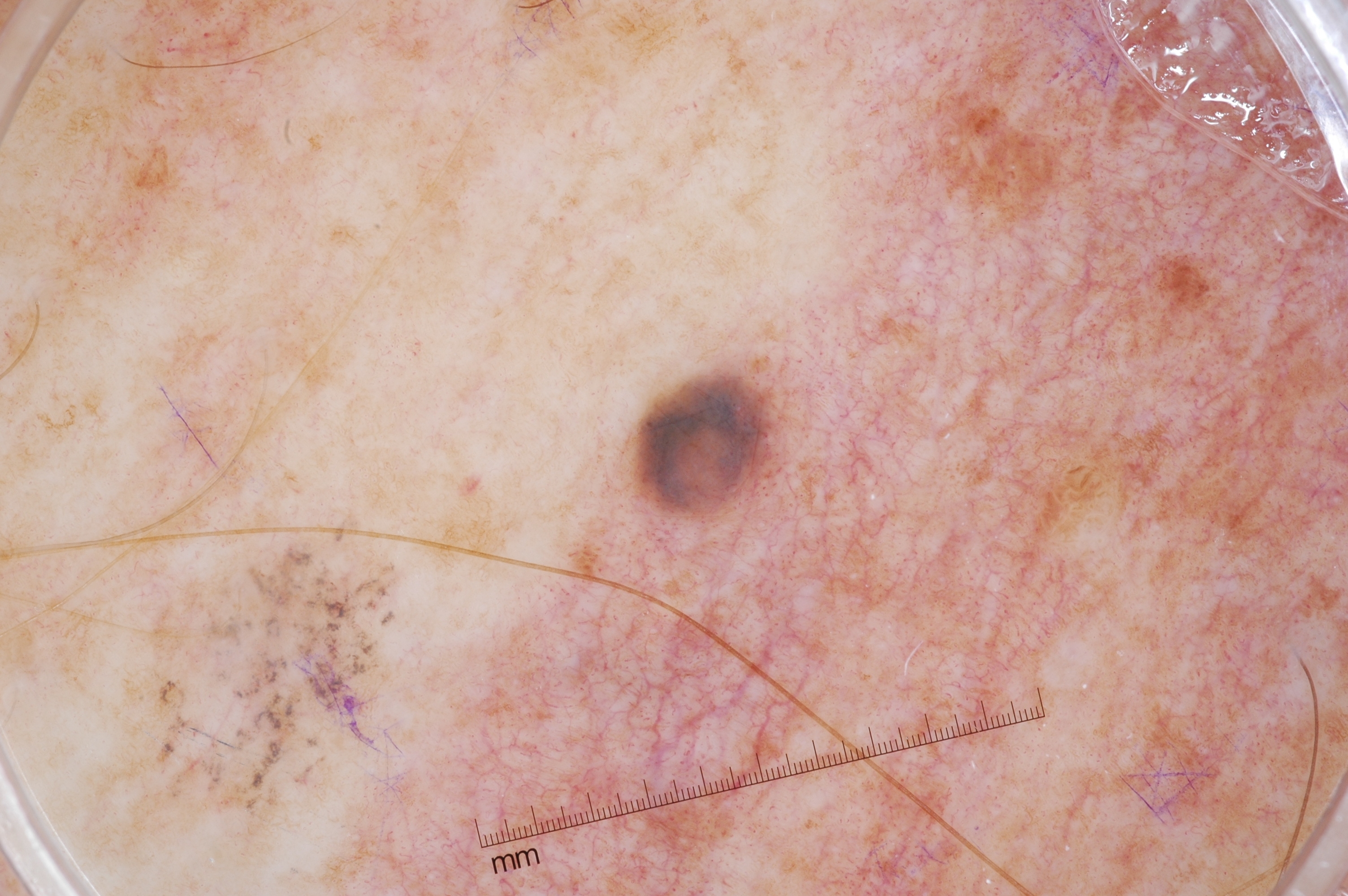– image type · dermoscopy
– patient · male, roughly 50 years of age
– location · bbox=[626, 369, 790, 523]
– lesion size · small
– absent dermoscopic findings · streaks, negative network, milia-like cysts, and pigment network
– assessment · a melanocytic nevus, a benign lesion